A female subject aged 33-37 · a dermoscopic image of a skin lesion.
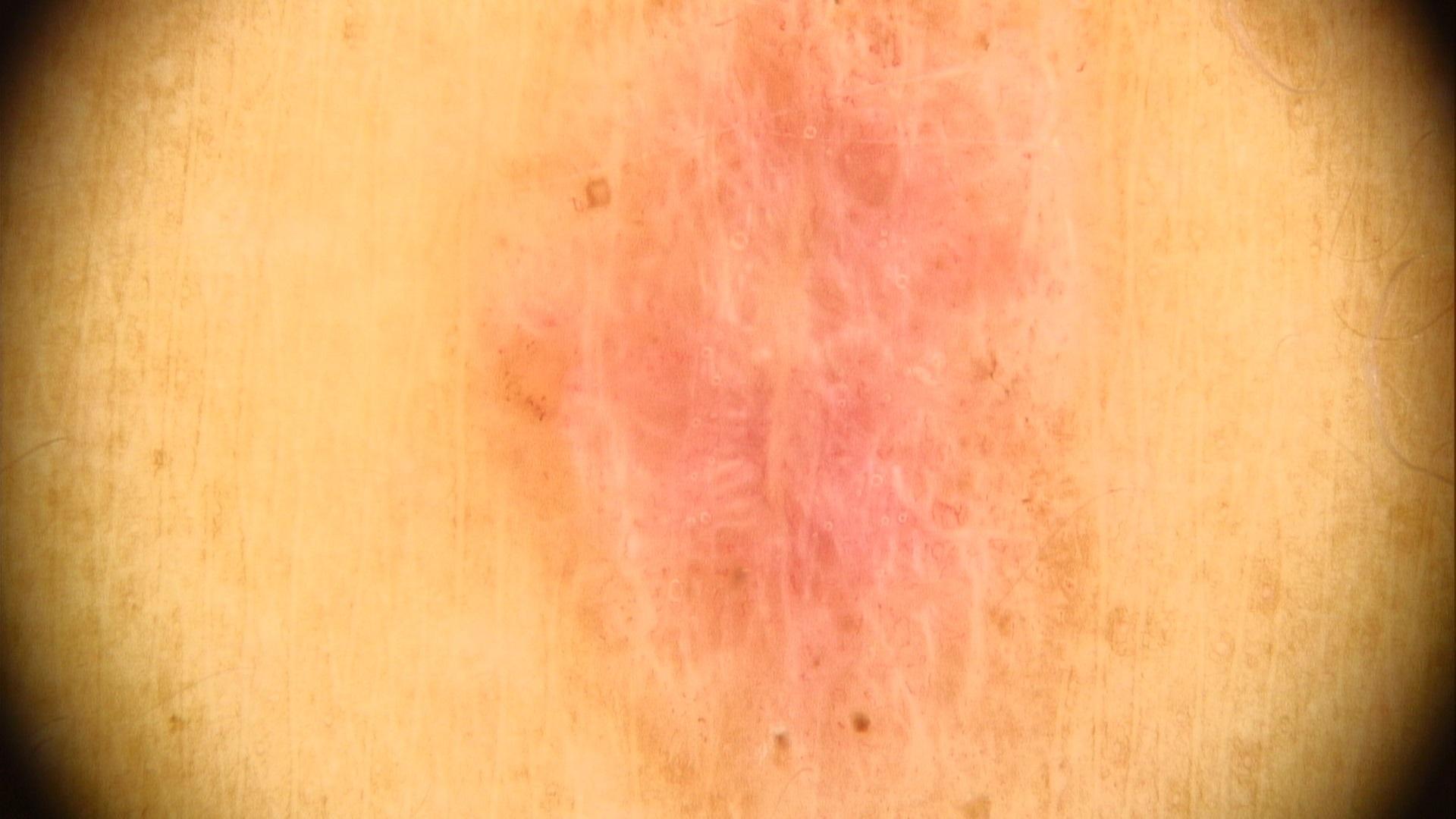Findings: The lesion was found on the trunk. Diagnosis: Histopathological examination showed a basal cell carcinoma.